An image taken at an angle; the lesion involves the head or neck:
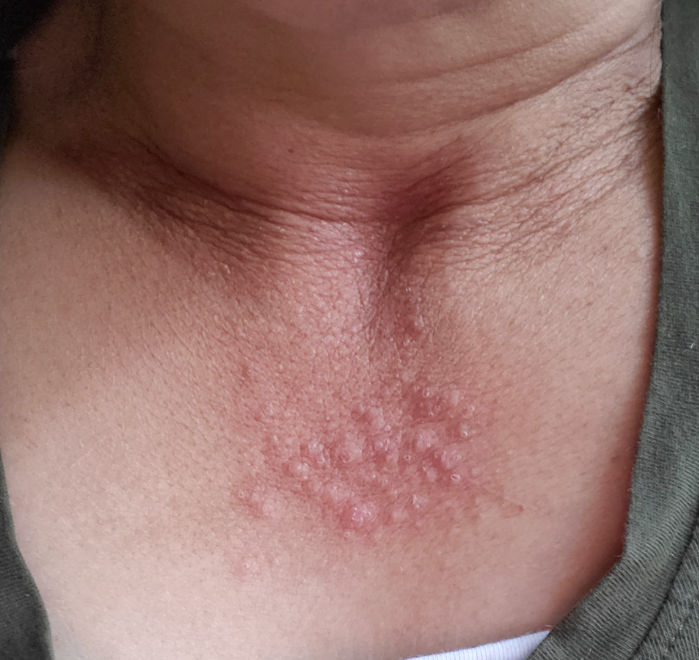History:
Skin tone: Fitzpatrick III; non-clinician graders estimated MST 3. Texture is reported as raised or bumpy. The contributor reports itching, pain and bothersome appearance. The condition has been present for less than one week.
Impression:
Most likely Cutaneous lupus.